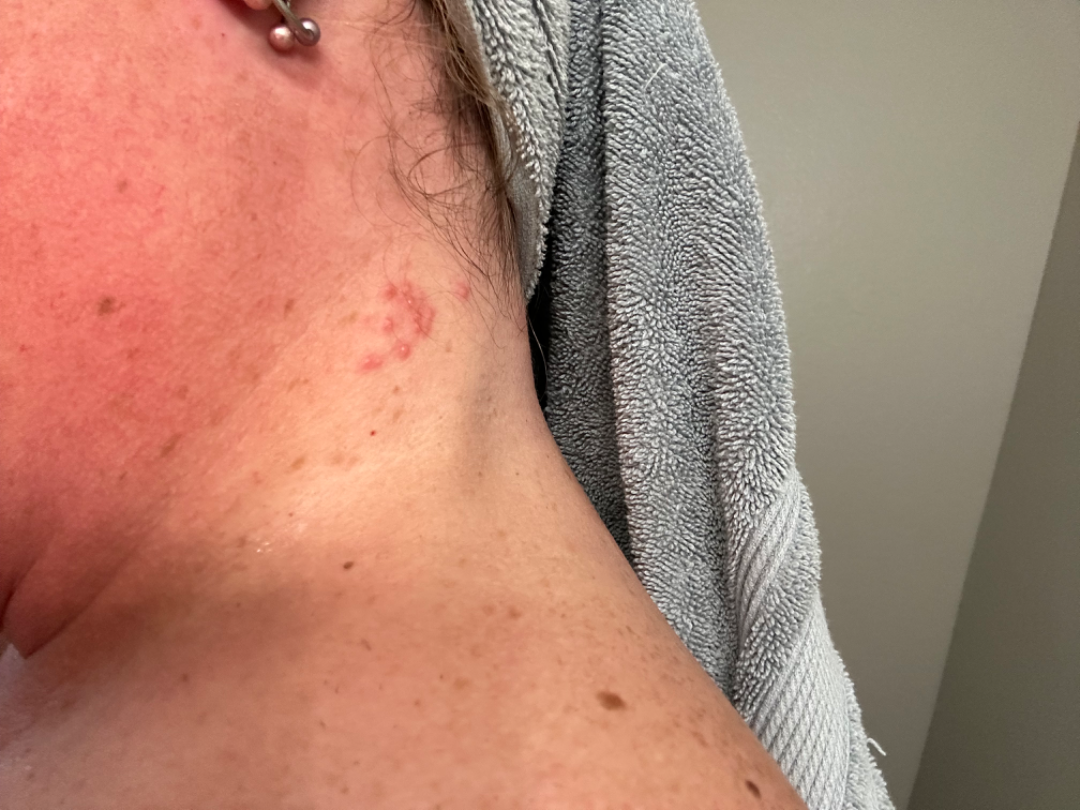{"shot_type": "at a distance", "patient": "female, age 40–49", "body_site": "head or neck", "differential": {"leading": ["Herpes Simplex"], "considered": ["Folliculitis"]}}